The patient is a female roughly 40 years of age, this is a dermoscopic photograph of a skin lesion:
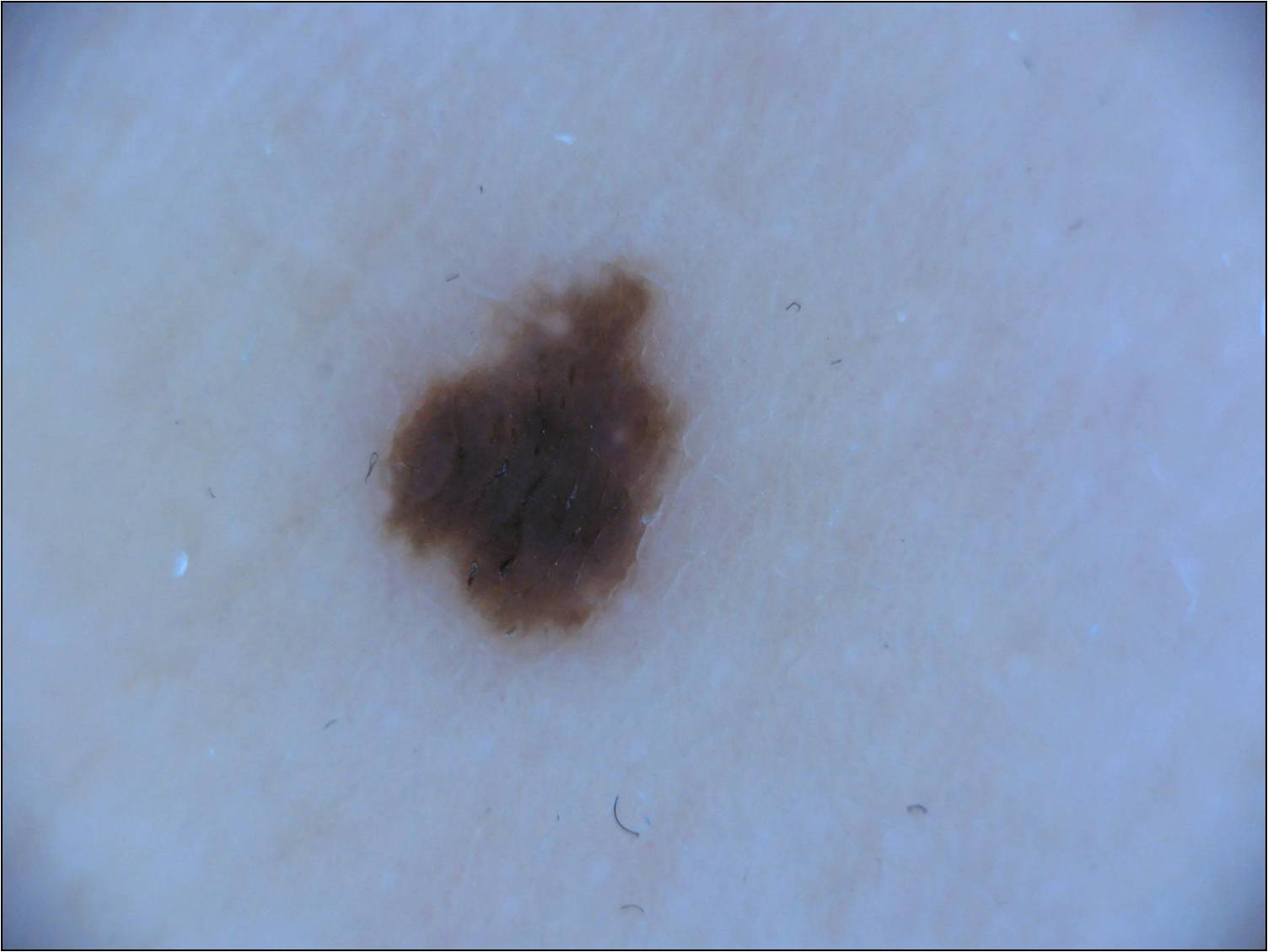  dermoscopic_features:
    present: []
    absent:
      - negative network
      - milia-like cysts
      - globules
      - pigment network
      - streaks
  lesion_location:
    bbox_xyxy:
      - 369
      - 260
      - 686
      - 644
  lesion_extent: small
  diagnosis:
    name: melanocytic nevus
    malignancy: benign
    lineage: melanocytic
    provenance: clinical